The photograph was taken at a distance. Skin tone: Fitzpatrick skin type III — 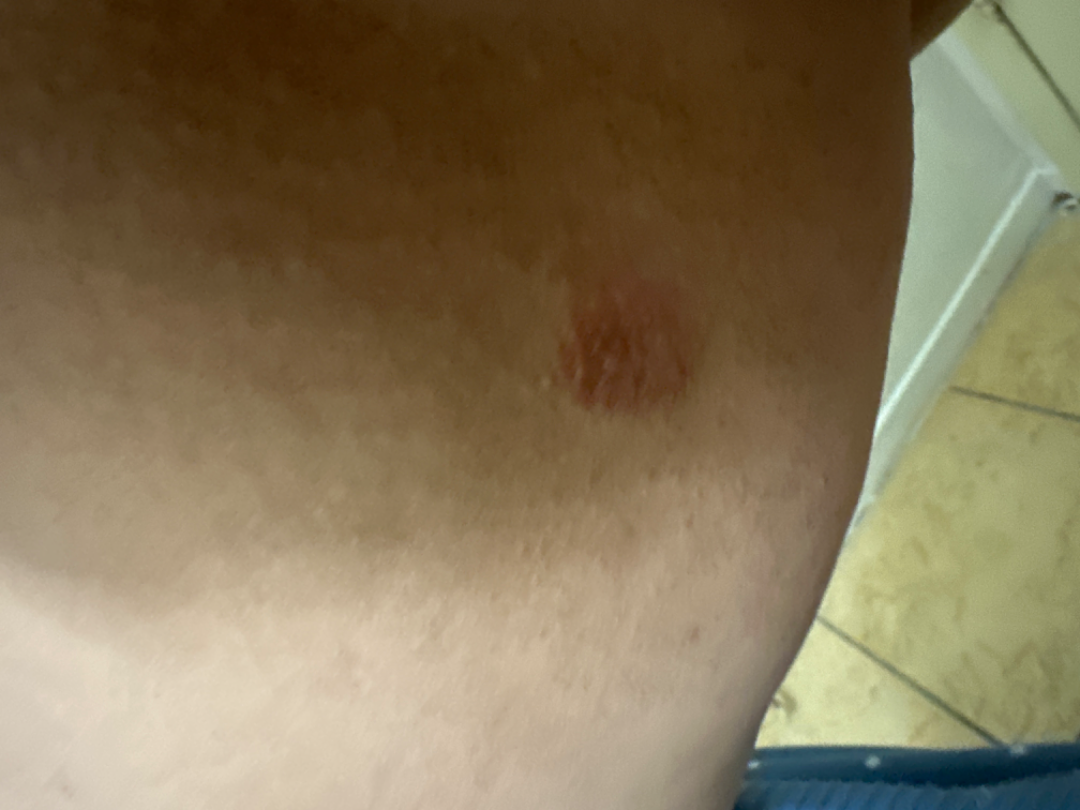{
  "assessment": "unable to determine"
}